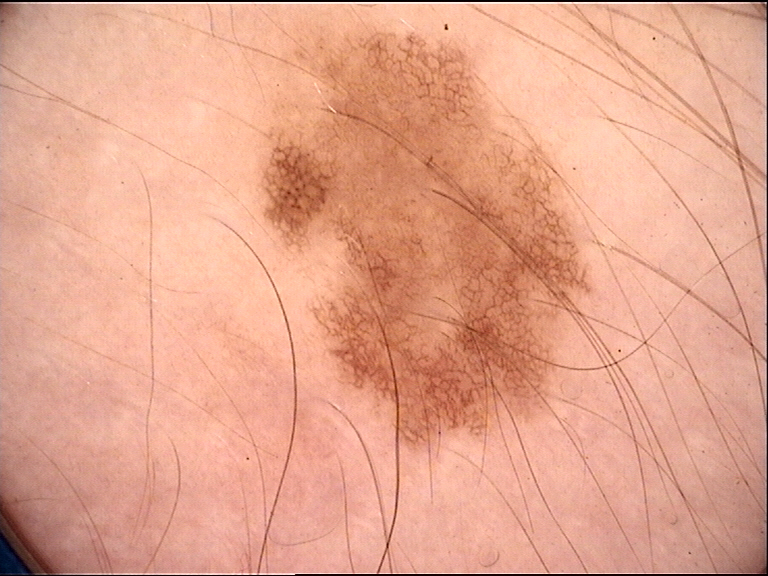The diagnostic label was a congenital junctional nevus.